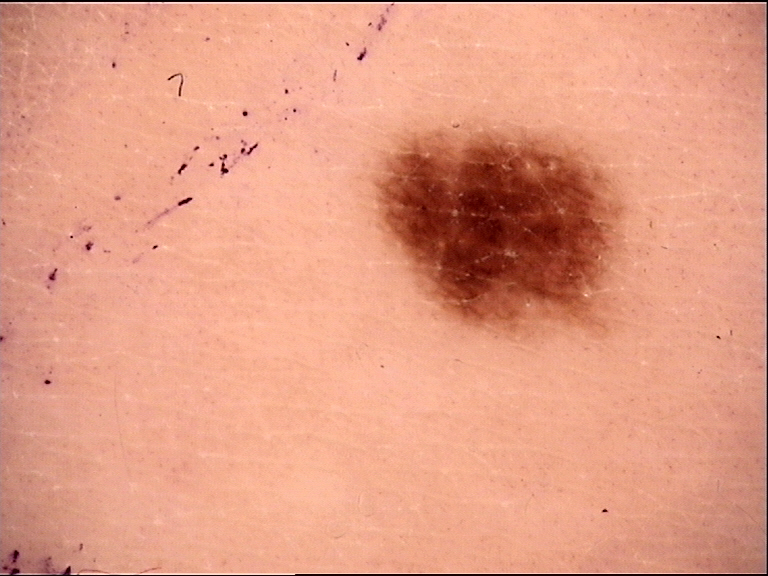image type = dermatoscopy
label = dysplastic junctional nevus (expert consensus)